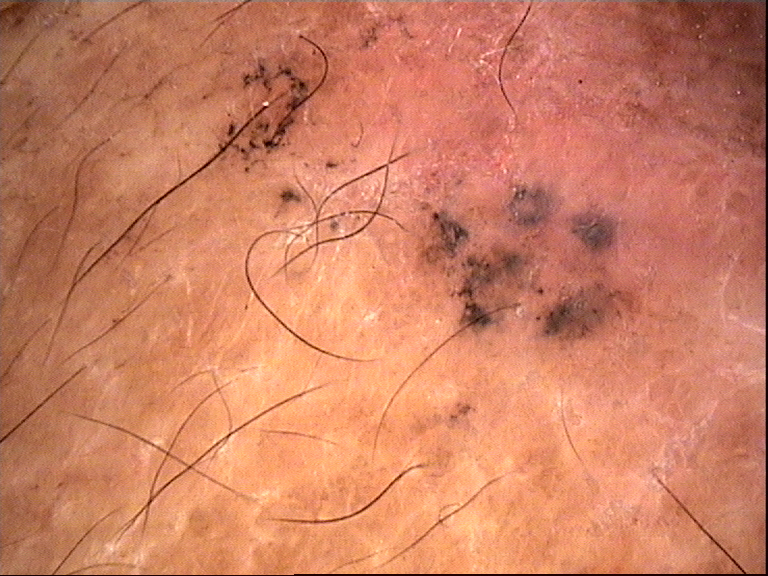Findings:
* imaging · dermatoscopy
* subtype · keratinocytic
* pathology · basal cell carcinoma (biopsy-proven)